The patient is a female roughly 40 years of age; dermoscopy of a skin lesion: 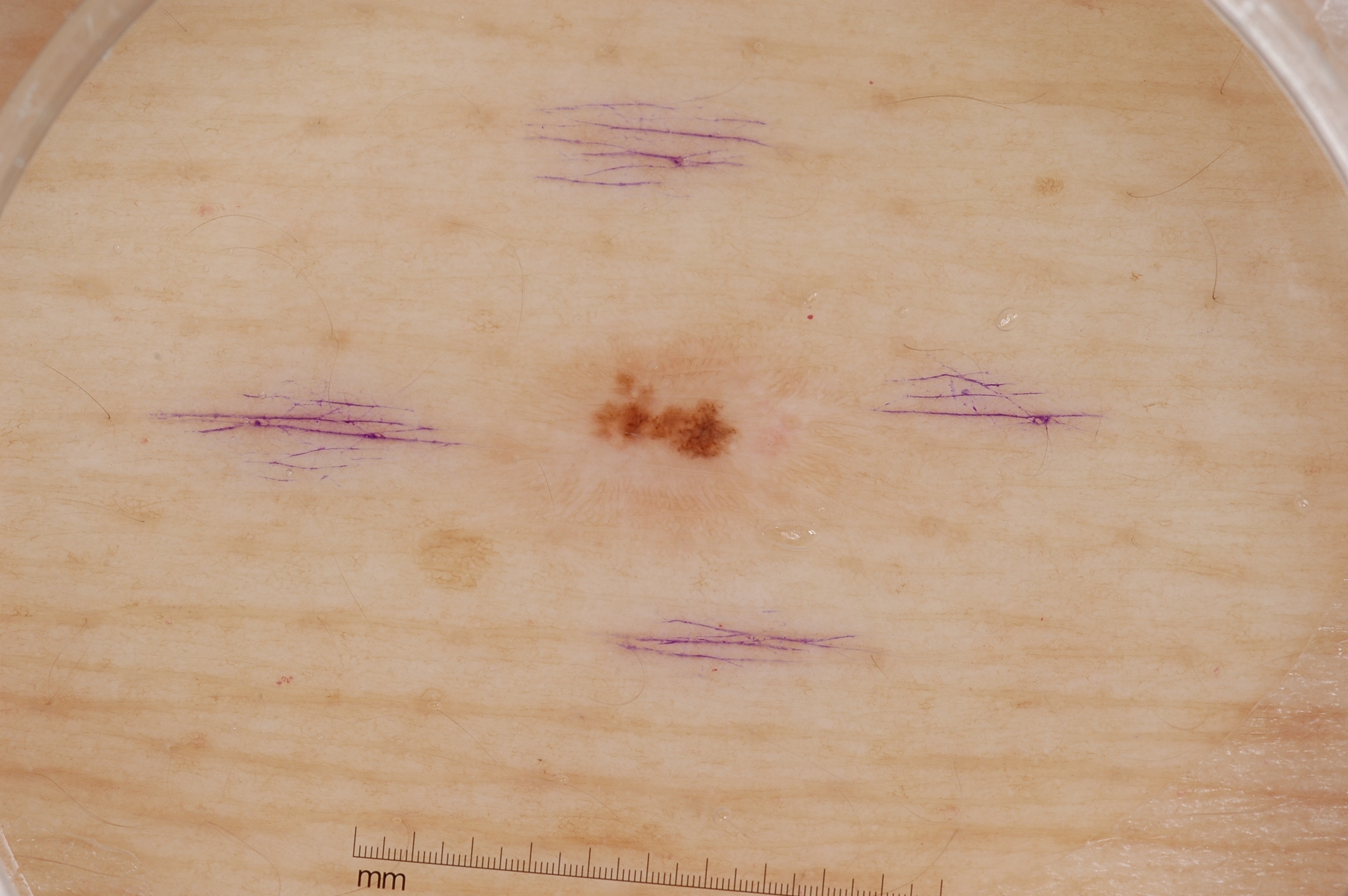As (left, top, right, bottom), the lesion is located at bbox=[488, 271, 875, 569]. Dermoscopy demonstrates no streaks, negative network, pigment network, or milia-like cysts. The lesion takes up about 7% of the image. The lesion was assessed as a melanocytic nevus, a benign skin lesion.